The lesion involves the arm, the photograph is a close-up of the affected area: 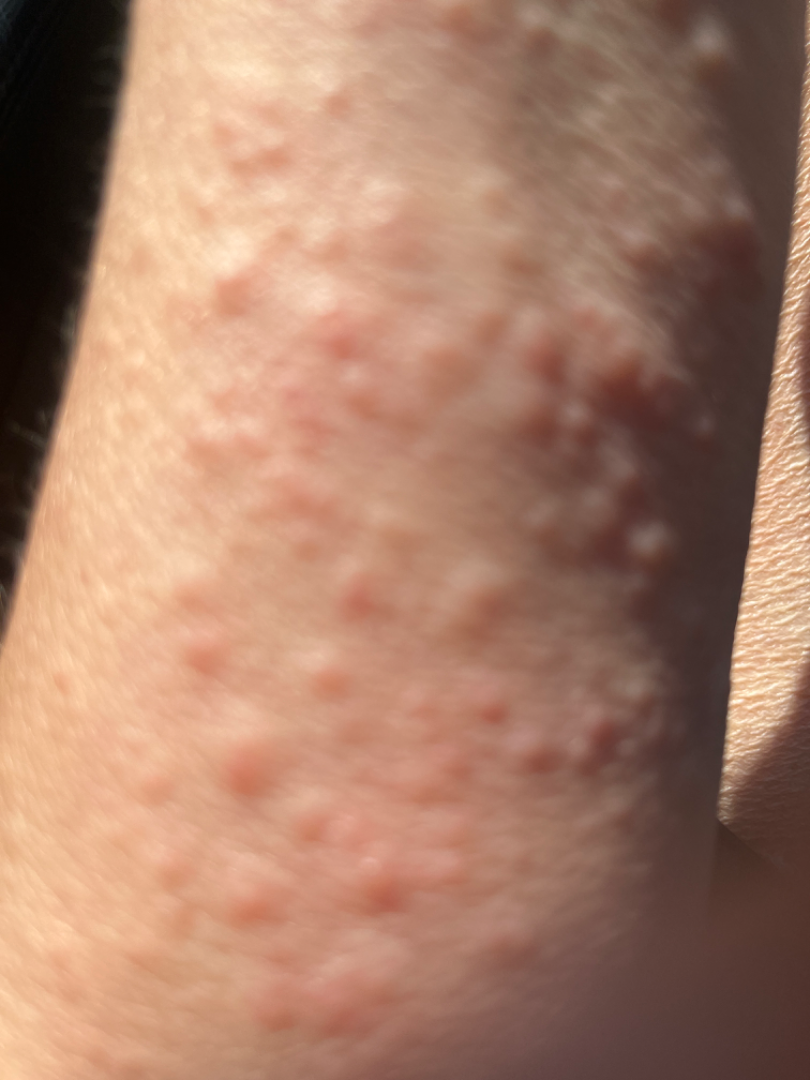History:
Symptoms reported: bothersome appearance.
Impression:
On dermatologist assessment of the image: most consistent with Allergic Contact Dermatitis.